Fitzpatrick II. The photograph is a close-up of the affected area: 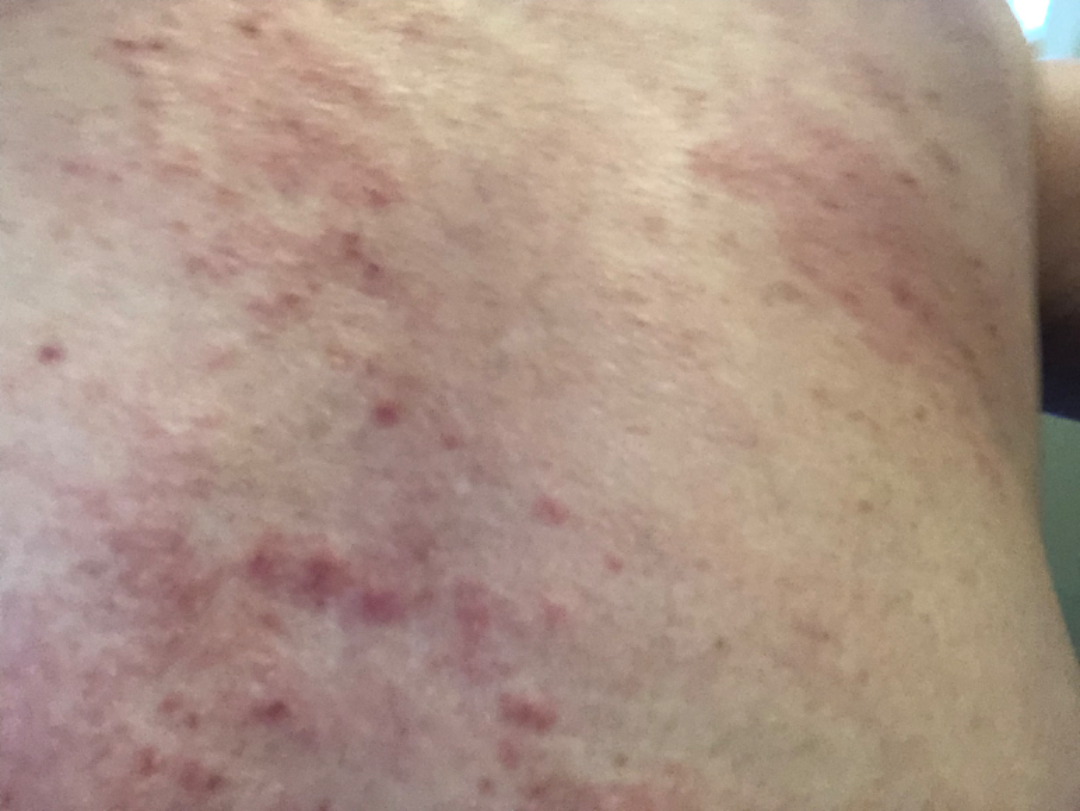{"differential": "Grover's disease"}